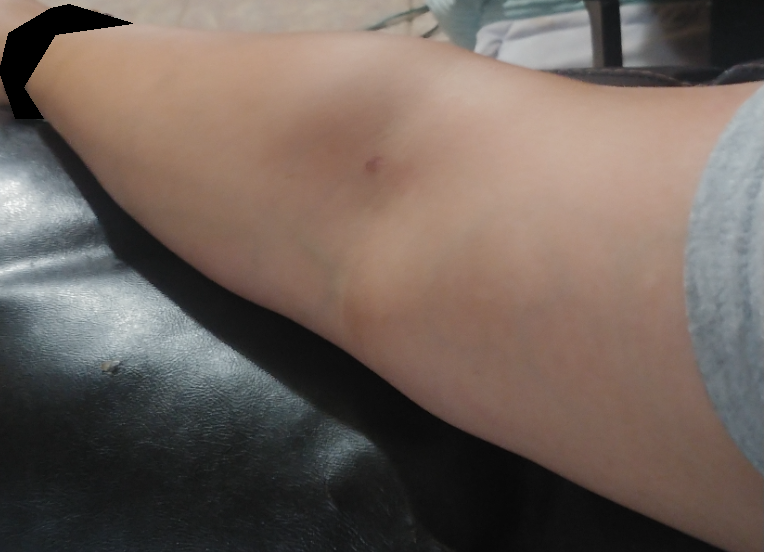Q: What was the assessment?
A: unable to determine